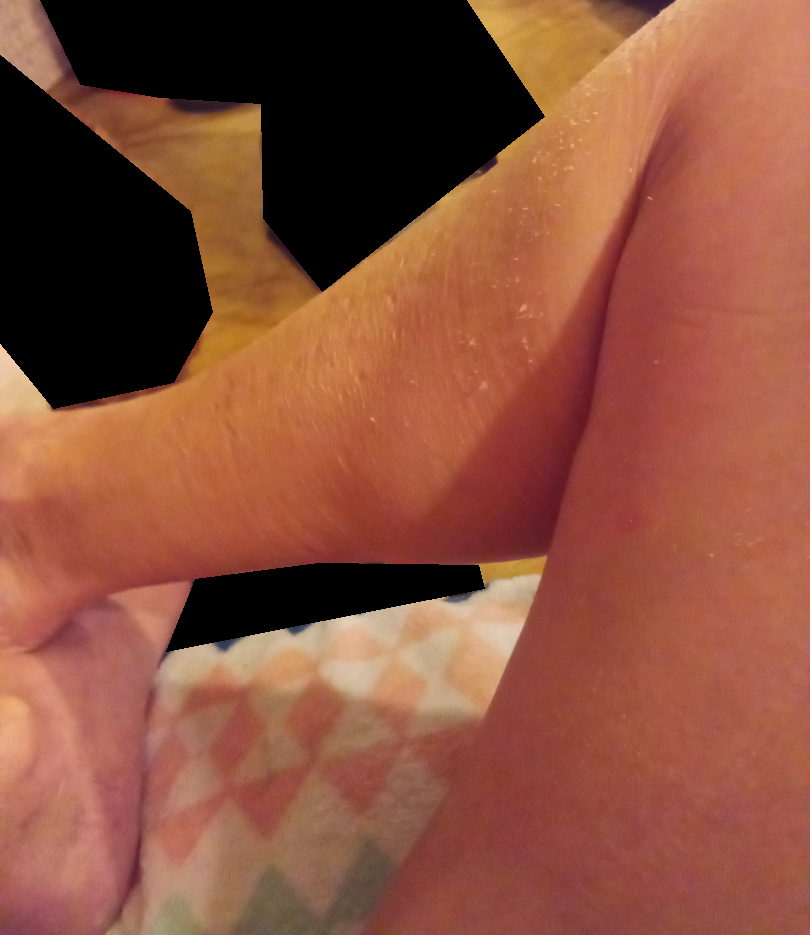This image was taken at a distance.
The reviewing clinician's impression was: Xerosis, Ichthyosis and Eczema were considered with similar weight.